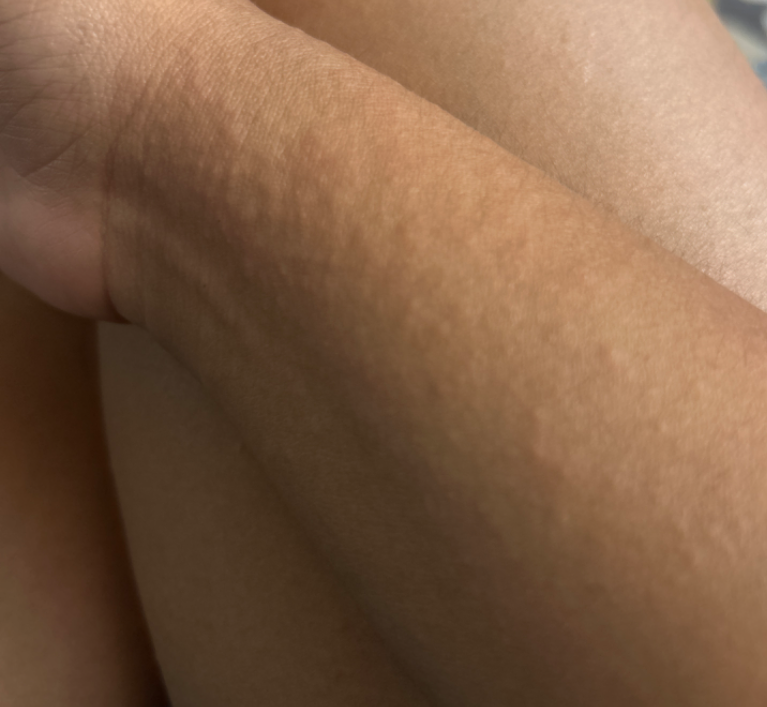Background: The patient notes the lesion is fluid-filled and raised or bumpy. No associated systemic symptoms reported. The lesion is associated with enlargement and itching. The subject is female. Located on the front of the torso, head or neck, back of the torso, arm and leg. This is a close-up image. Present for less than one week. Findings: Three independent reviewers: most likely Allergic Contact Dermatitis; also consider Acute dermatitis, NOS; a remote consideration is Miliaria; less probable is Hypersensitivity; less likely is Eczema.